The photograph is a close-up of the affected area · the lesion involves the leg, front of the torso and arm: 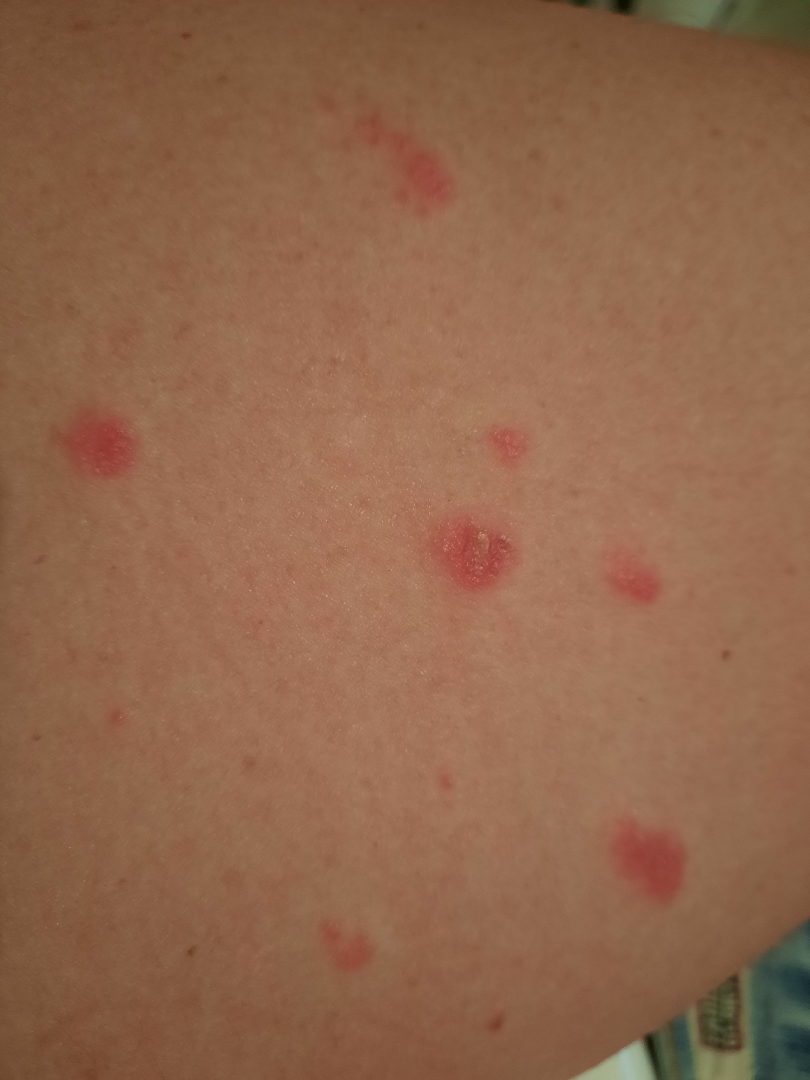Findings:
• clinical impression — the differential includes Psoriasis, Eczema and Allergic Contact Dermatitis, with no clear leading consideration